Dermoscopy of a skin lesion · acquired for a research image collection, with no referral diagnosis · a female subject aged 75.
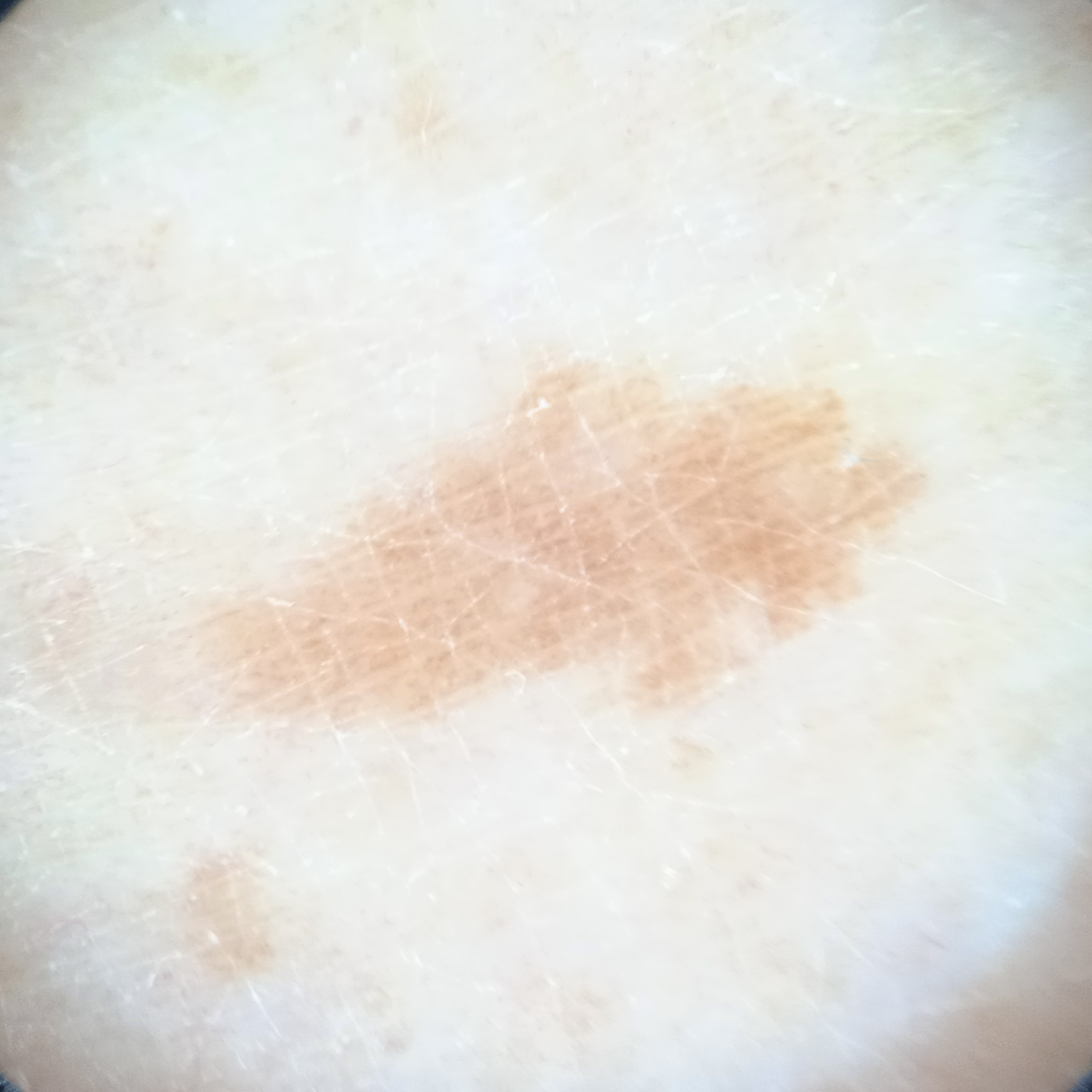lesion_location: a leg
diagnosis:
  name: melanocytic nevus
  malignancy: benign